A male patient, in their 60s; a dermoscopy image of a single skin lesion: 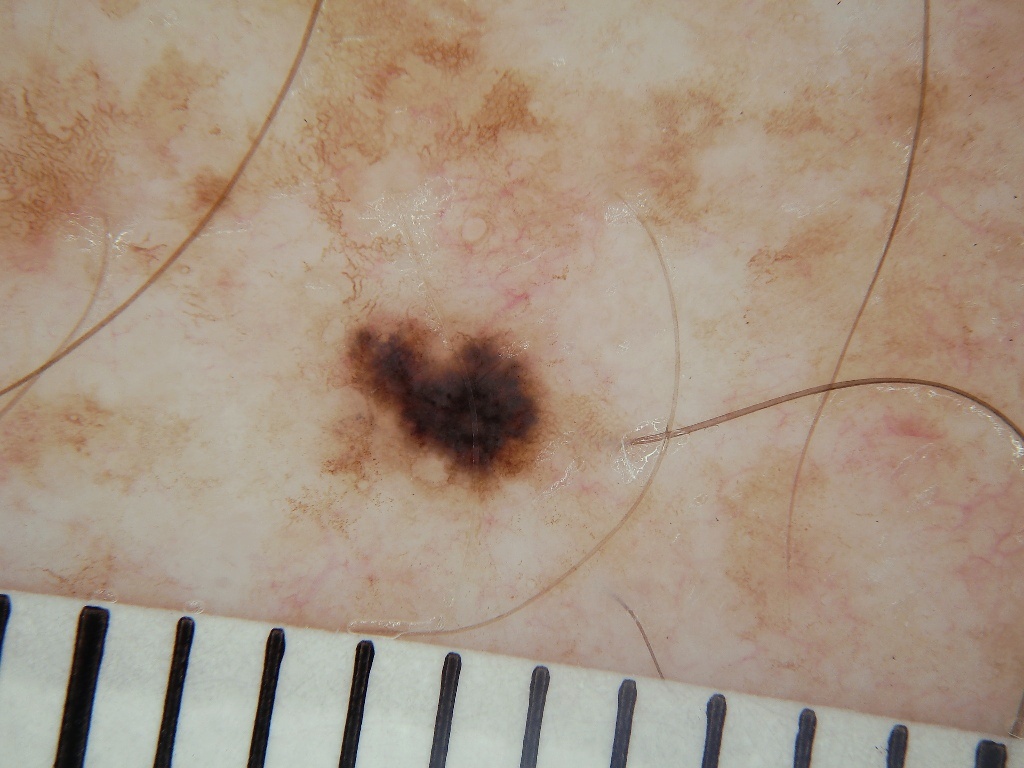Q: What does dermoscopy show?
A: pigment network; absent: globules, milia-like cysts, streaks, and negative network
Q: What is the lesion's bounding box?
A: <bbox>329, 311, 557, 498</bbox>
Q: How large is the lesion within the image?
A: ~4% of the field
Q: What is this lesion?
A: a melanocytic nevus